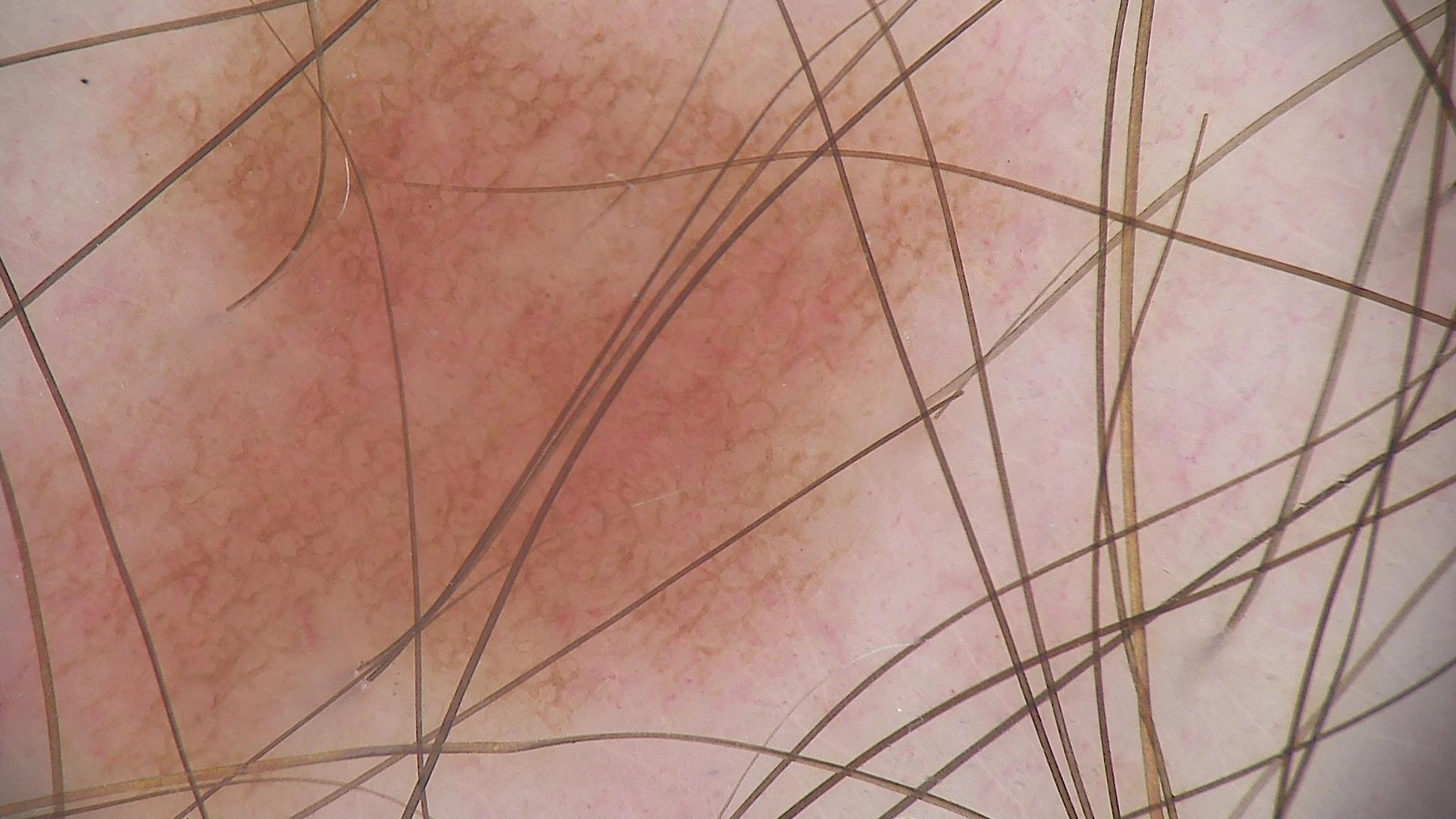Labeled as a dysplastic junctional nevus.